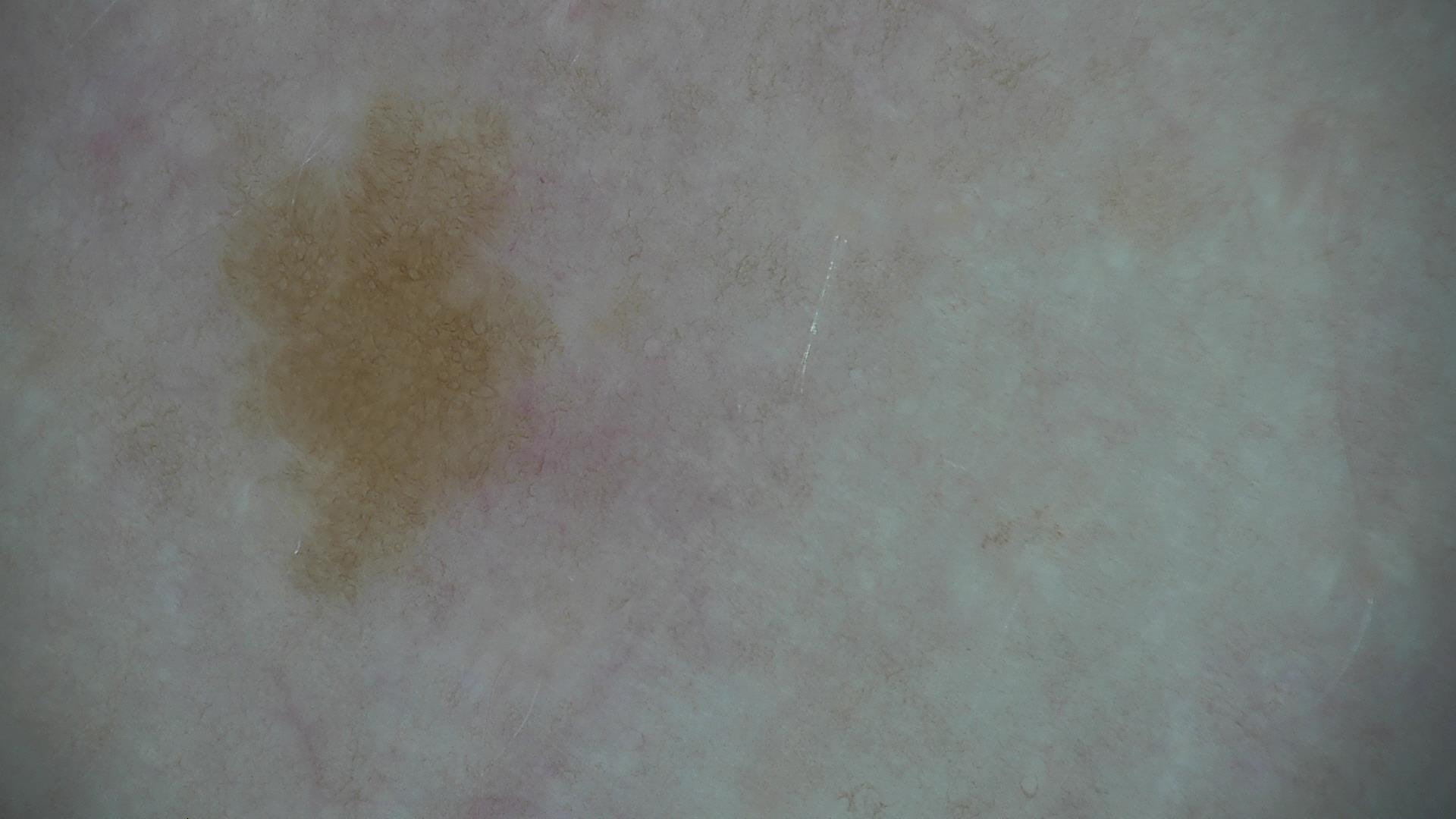Conclusion:
The diagnostic label was a benign lesion — a solar lentigo.